A dermoscopic photograph of a skin lesion:
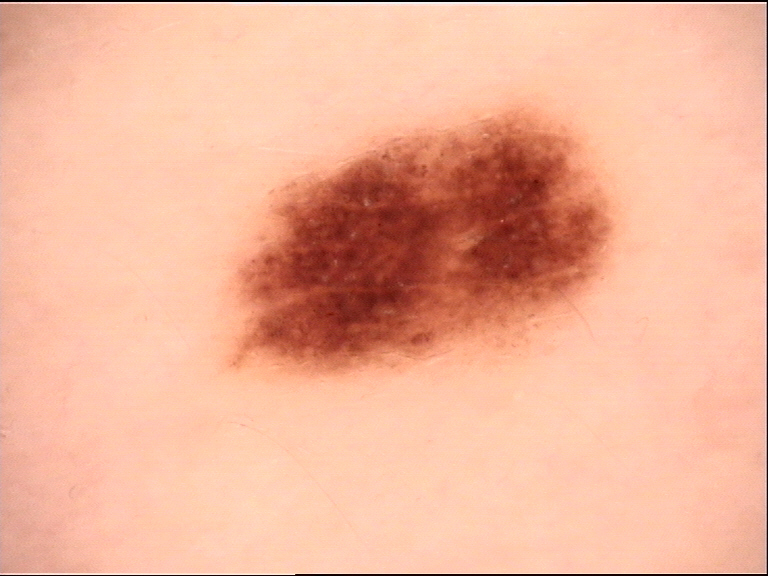* diagnostic label · dysplastic junctional nevus (expert consensus)